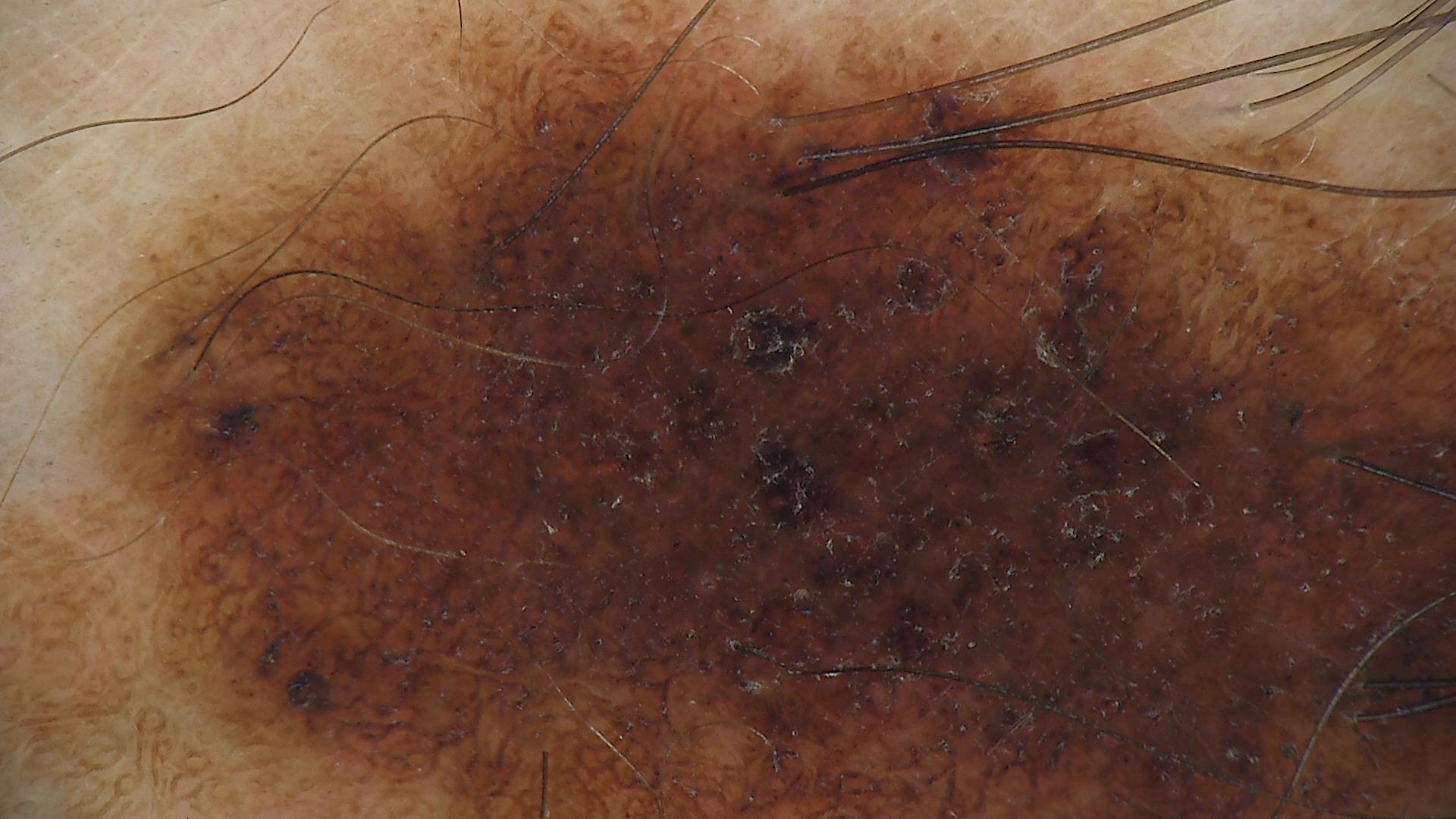image type = dermoscopy | assessment = congenital dysplastic compound nevus (expert consensus).